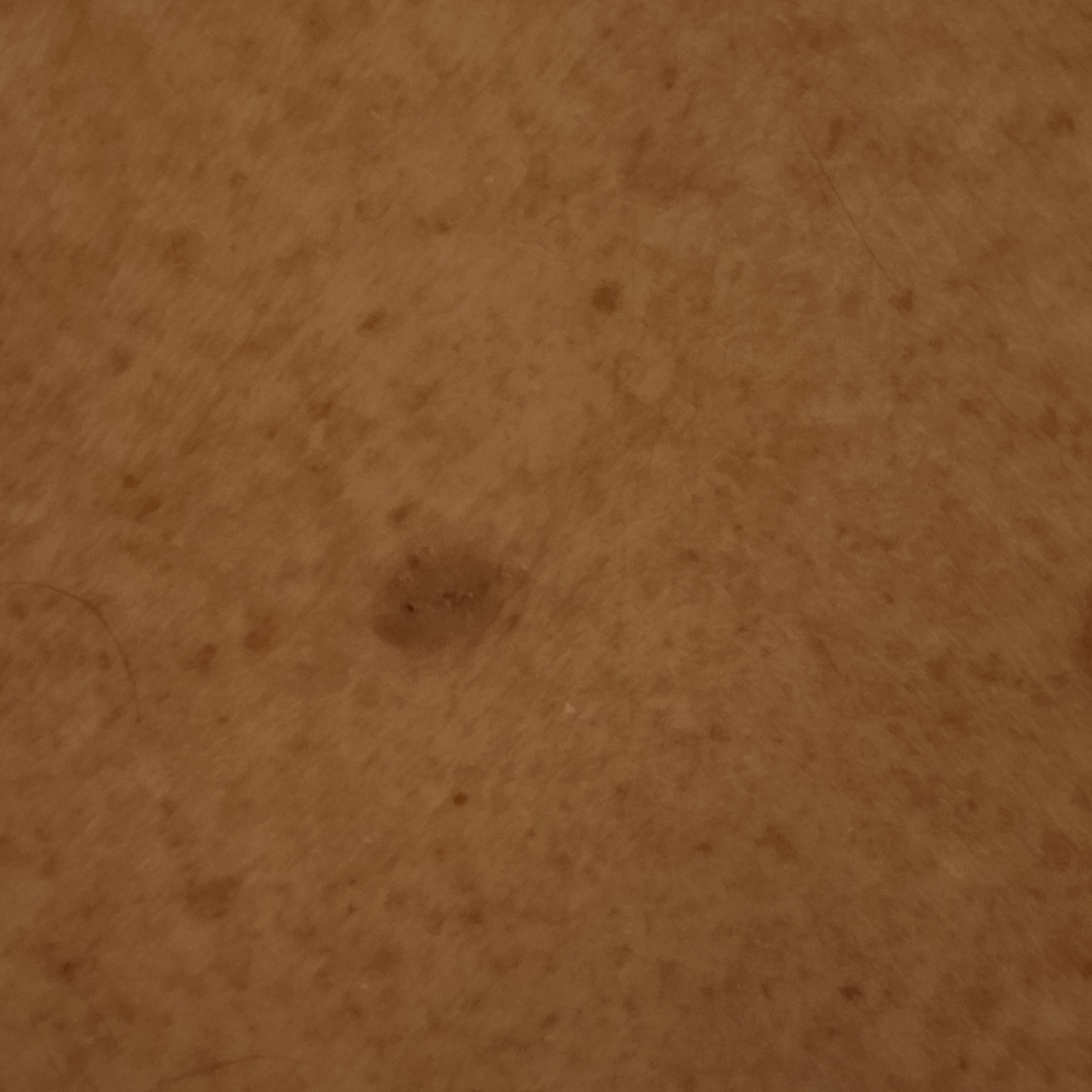Case summary: The patient says their skin reddens with sun exposure. Collected as part of a research study, without a referral diagnosis. A male subject aged 66. Few moles overall by the patient's own estimate. On a questionnaire the patient reported no family history of skin cancer and no sunbed use. A clinical photograph showing a skin lesion. Measuring roughly 9.5 mm. Conclusion: The diagnostic impression was a seborrheic keratosis.